The photo was captured at a distance; the affected area is the leg; the patient is 18–29, female — 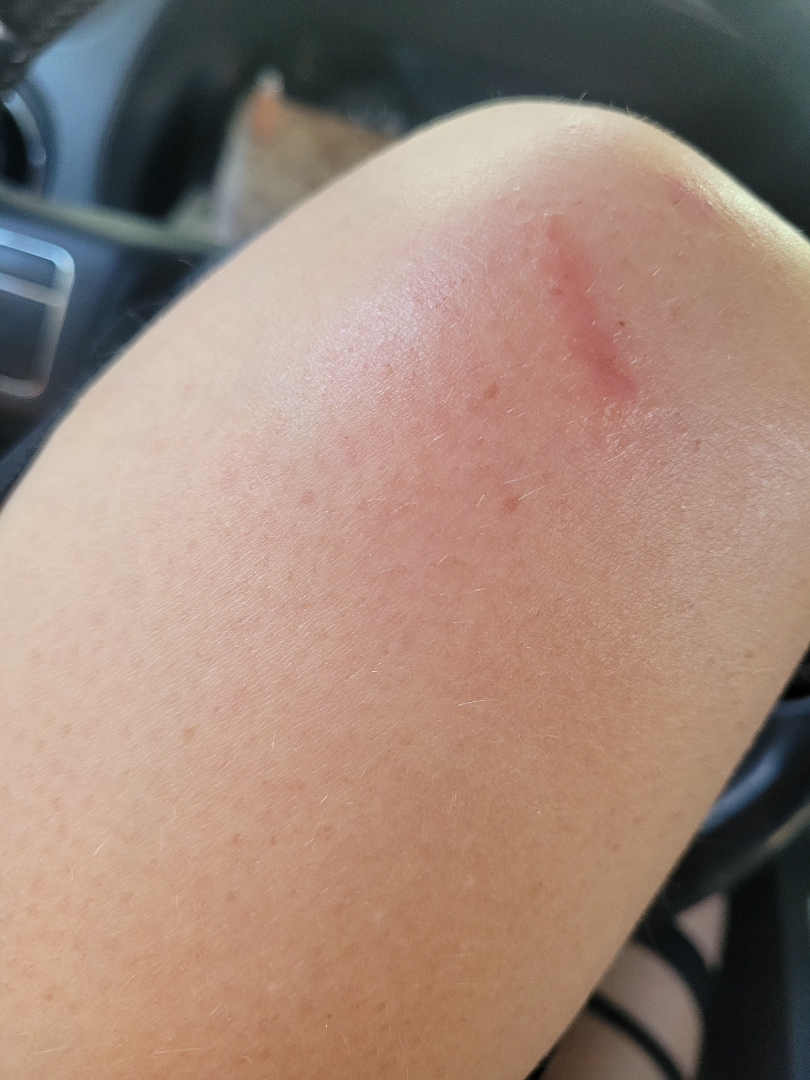Review:
The reviewing dermatologist was unable to assign a differential diagnosis from the image.